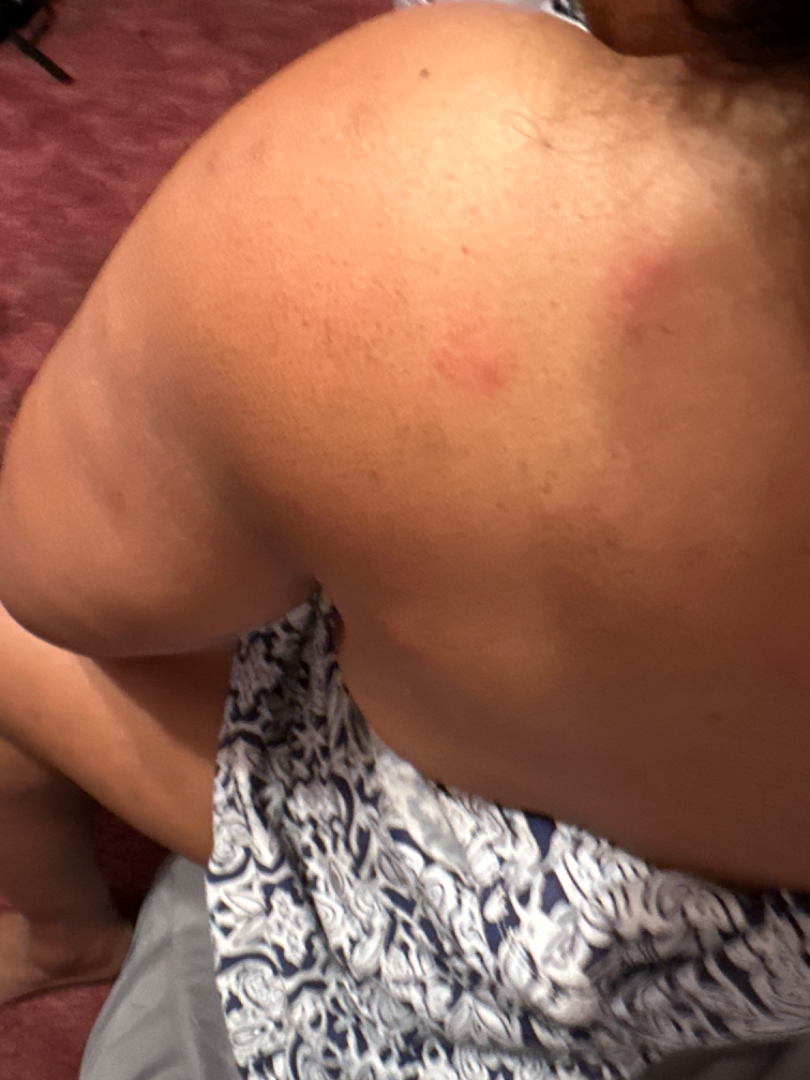The case was difficult to assess from the available photograph. Human graders estimated a MST of 4. Texture is reported as raised or bumpy. The patient considered this a rash. The front of the torso, leg, arm and head or neck are involved. No constitutional symptoms were reported. This is a close-up image. The contributor is 50–59, female. Reported lesion symptoms include bothersome appearance and itching. The patient indicates the condition has been present for one to four weeks.